A dermoscopic close-up of a skin lesion: 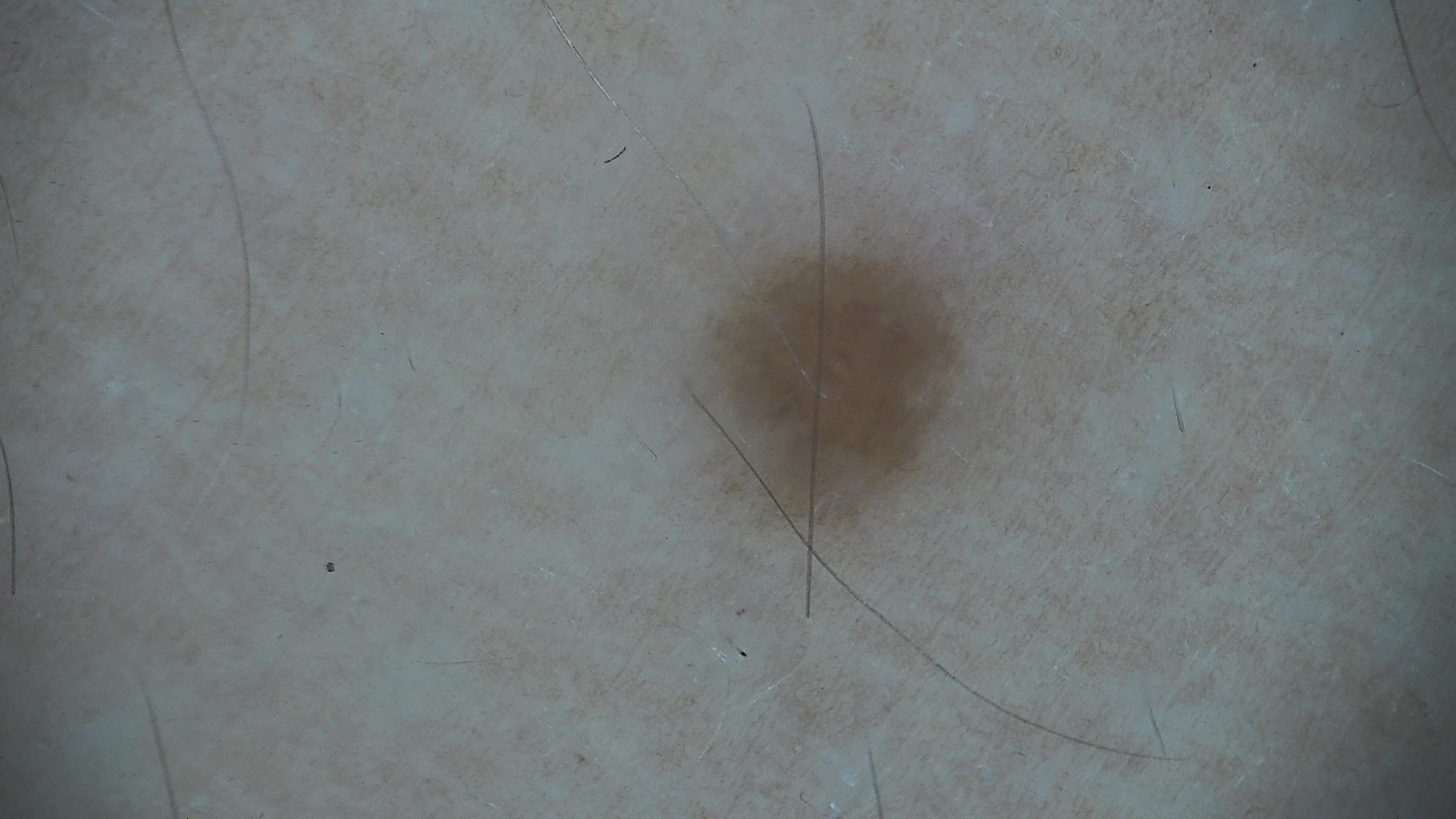Consistent with a dysplastic junctional nevus.